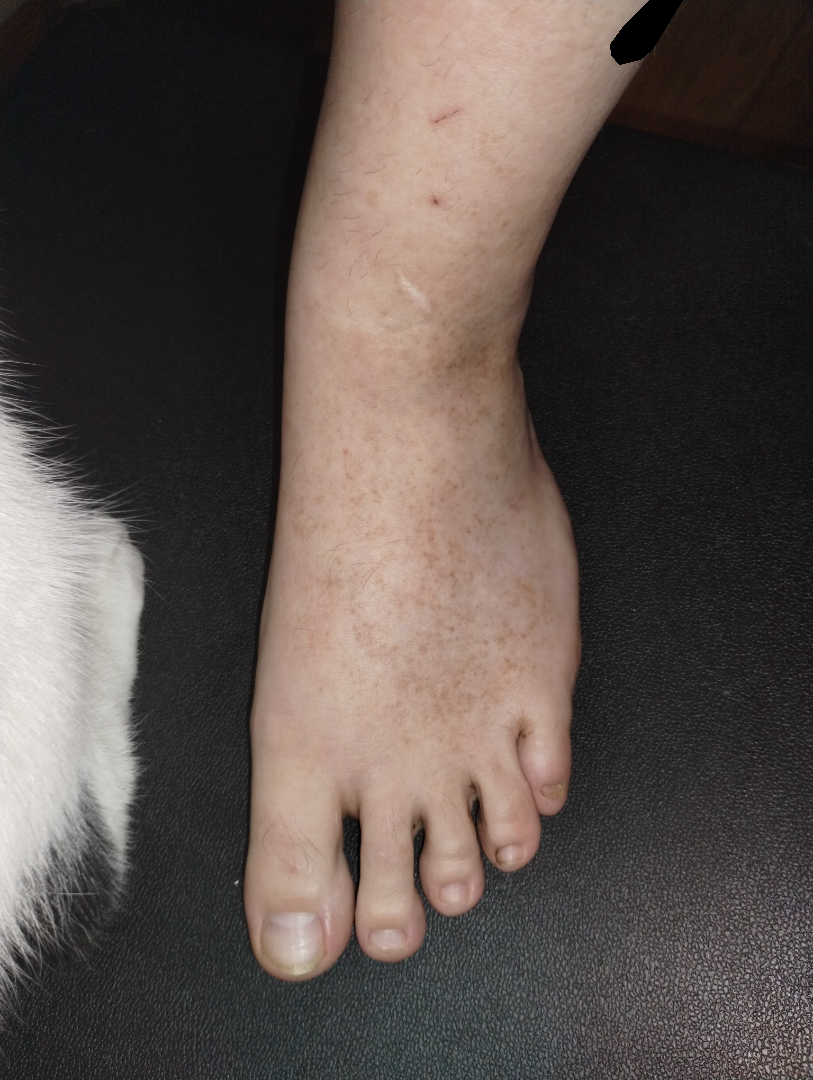The affected area is the top or side of the foot and leg.
Female contributor, age 18–29.
This image was taken at a distance.
Hemosiderin pigmentation of lower limb due to varicose veins of lower limb (favored); Pigmented purpuric eruption (possible).